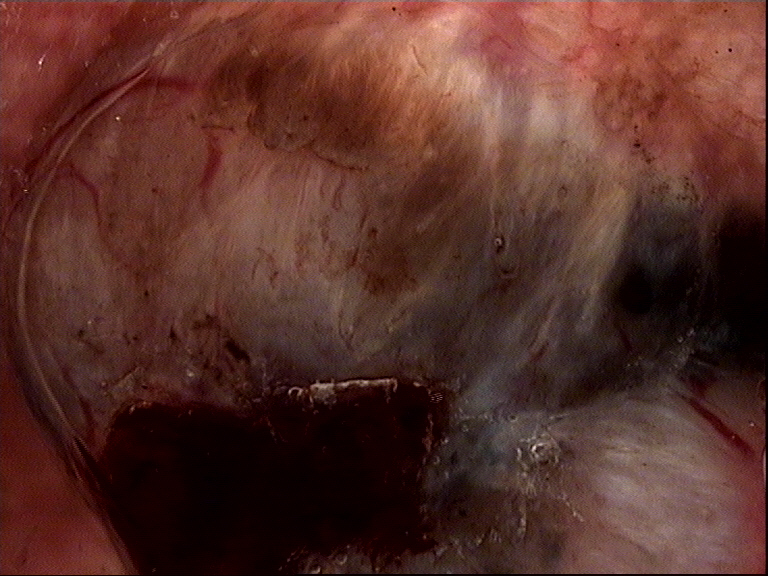A dermatoscopic image of a skin lesion.
The biopsy diagnosis was a keratinocytic lesion — a basal cell carcinoma.